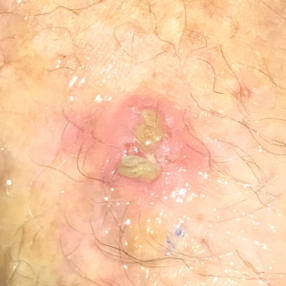Findings:
- patient: female, age 83
- exposures: prior skin cancer (patient or family)
- FST: II
- imaging: smartphone clinical photo
- anatomic site: a forearm
- size: 10x8 mm
- diagnosis: actinic keratosis (biopsy-proven)